The photograph was taken at an angle. Reported lesion symptoms include bothersome appearance. The contributor is a female aged 18–29. The lesion is described as flat. The affected area is the leg. Present for about one day: 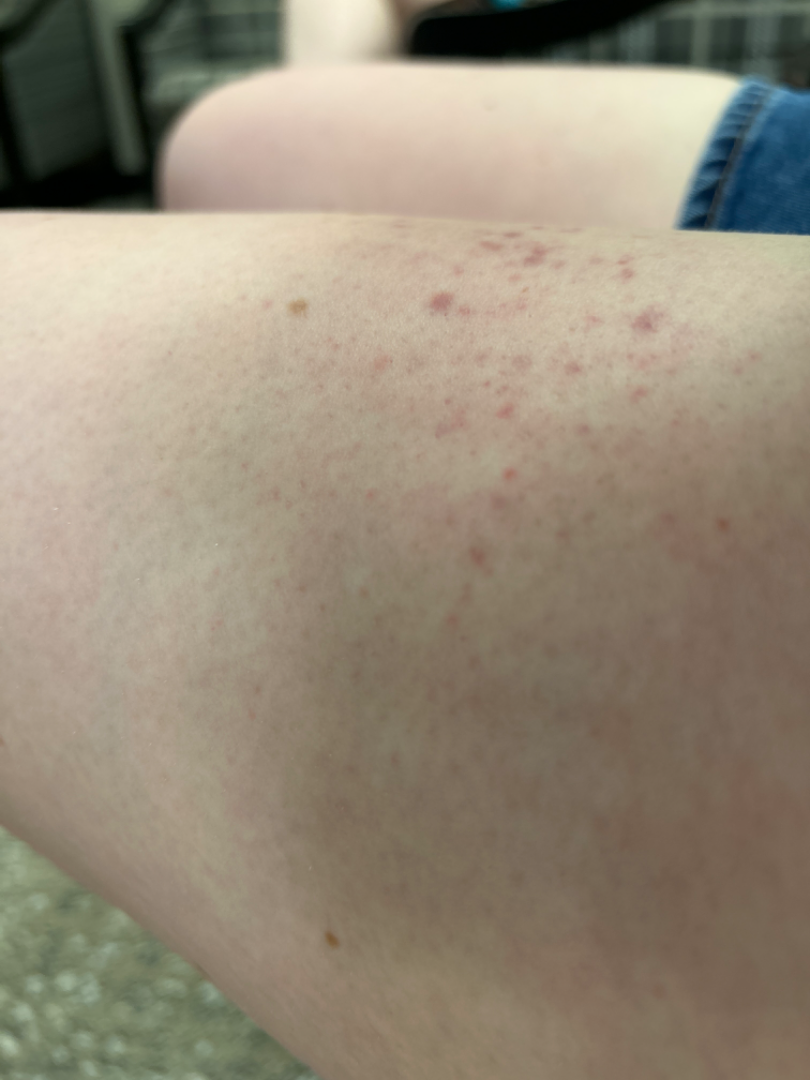Review:
On remote dermatologist review: Purpura (leading).